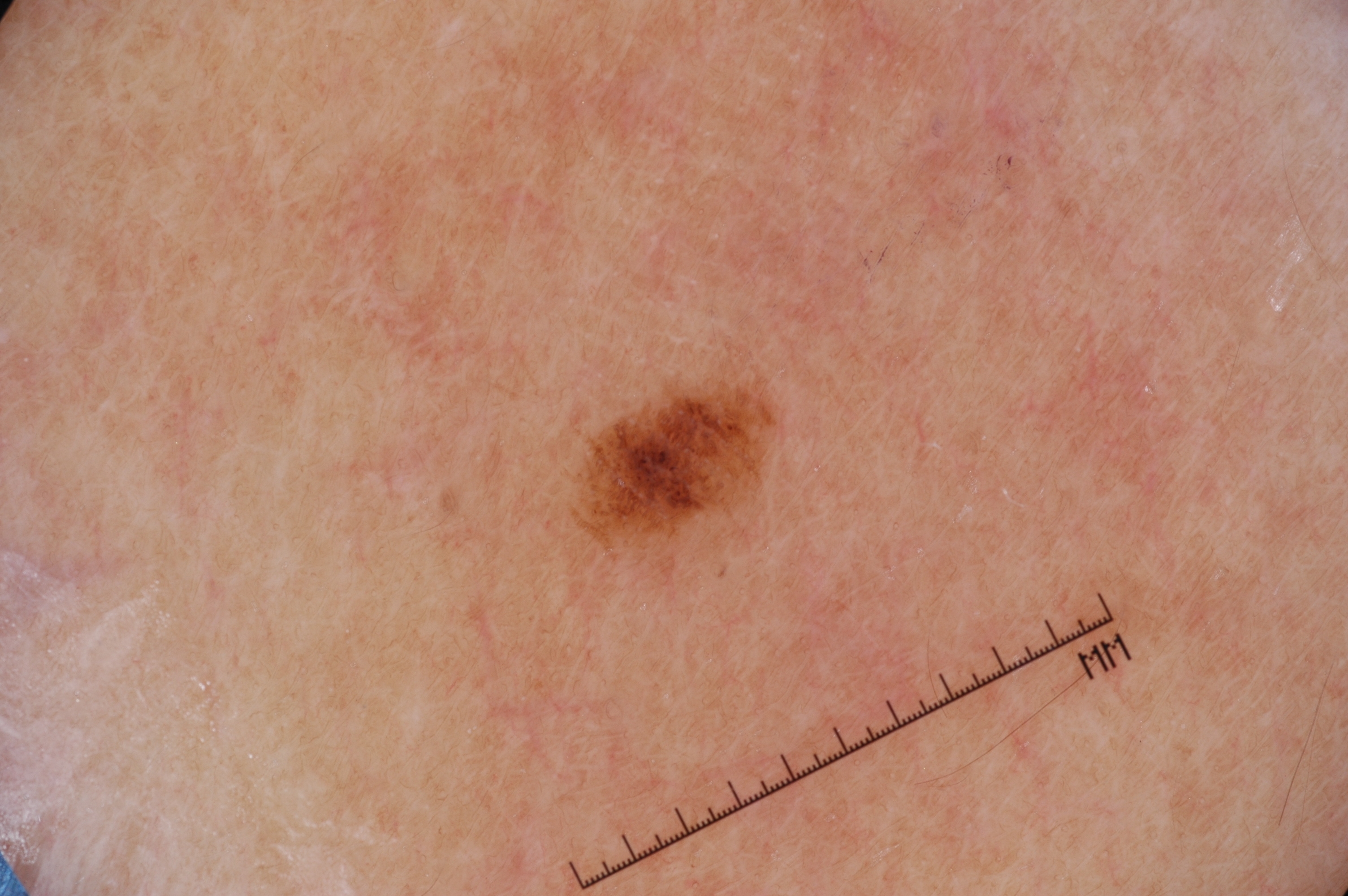patient: female, in their 40s | modality: dermoscopy of a skin lesion | dermoscopic features assessed but absent: negative network, streaks, milia-like cysts, and pigment network | lesion extent: small | lesion bbox: (577, 381, 776, 551) | diagnosis: a melanocytic nevus, a benign lesion.